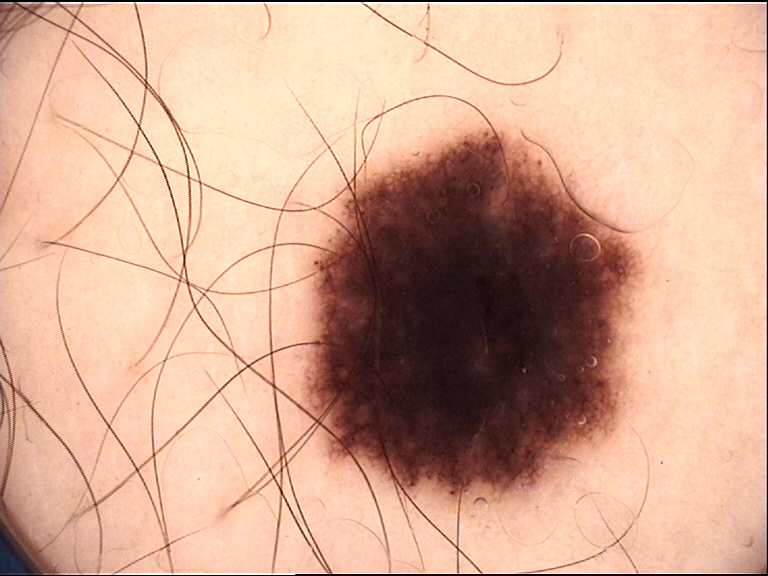Summary: A dermatoscopic image of a skin lesion. Impression: The diagnostic label was a dysplastic junctional nevus.